A dermoscopic close-up of a skin lesion · a female subject aged 73-77: 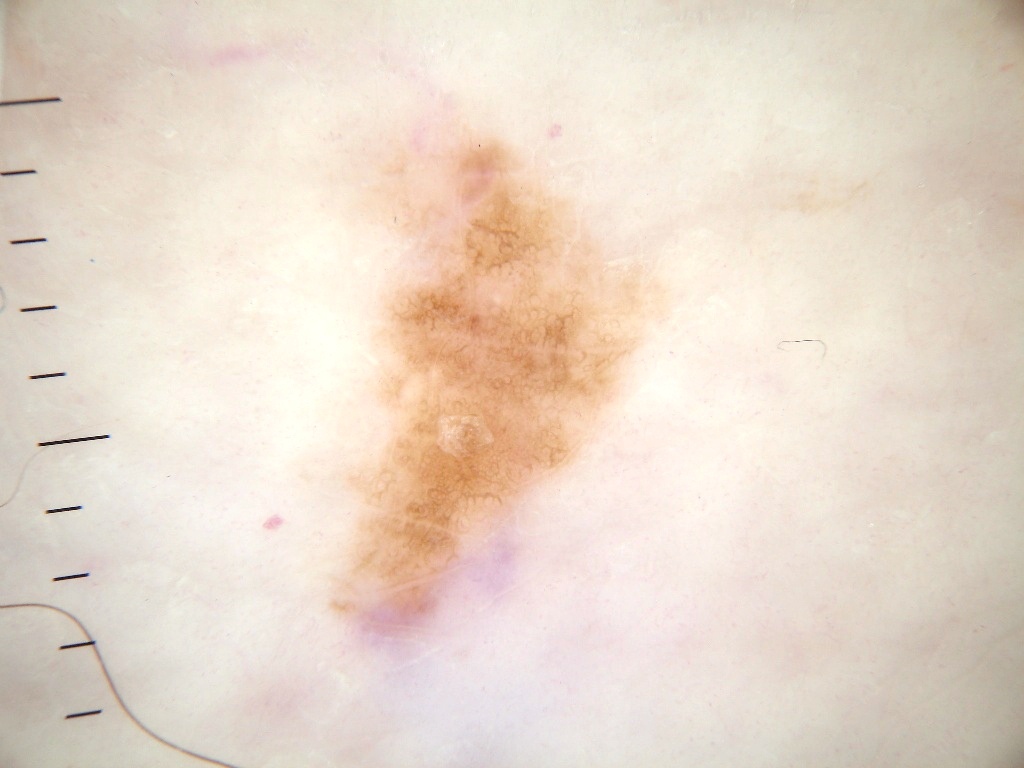location = bbox(324, 113, 667, 655) | dermoscopic findings = pigment network; absent: streaks, negative network, globules, and milia-like cysts | extent = moderate | diagnosis = a melanocytic nevus, a benign lesion.